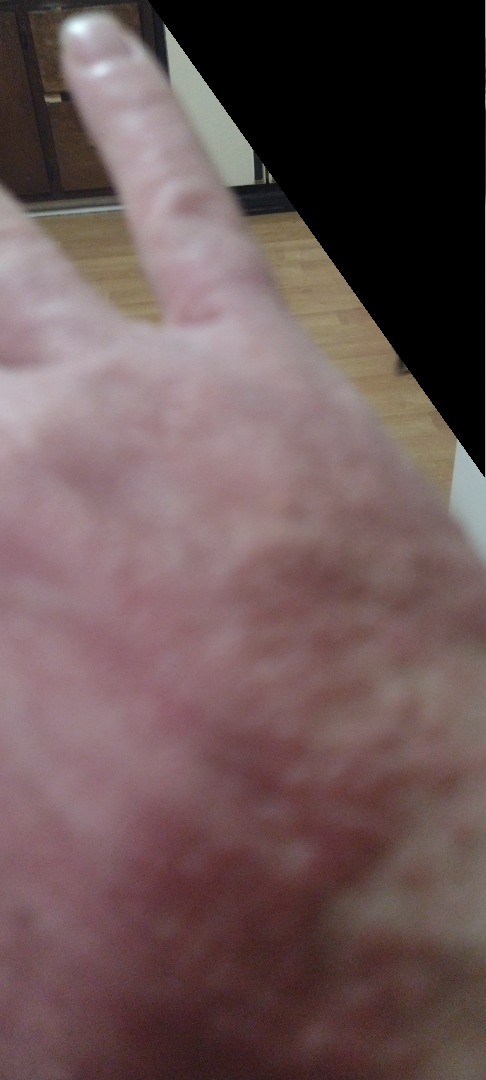This image was taken at a distance.
Skin tone: Fitzpatrick I; lay graders estimated Monk skin tone scale 2.
One reviewing dermatologist: the differential, in no particular order, includes Eczema and Allergic Contact Dermatitis.